A female subject age 78. By self-report, no immunosuppression and no sunbed use. Imaged for a research study, with no referral diagnosis recorded. The patient describes having numerous moles. The patient says their skin tans without first burning:
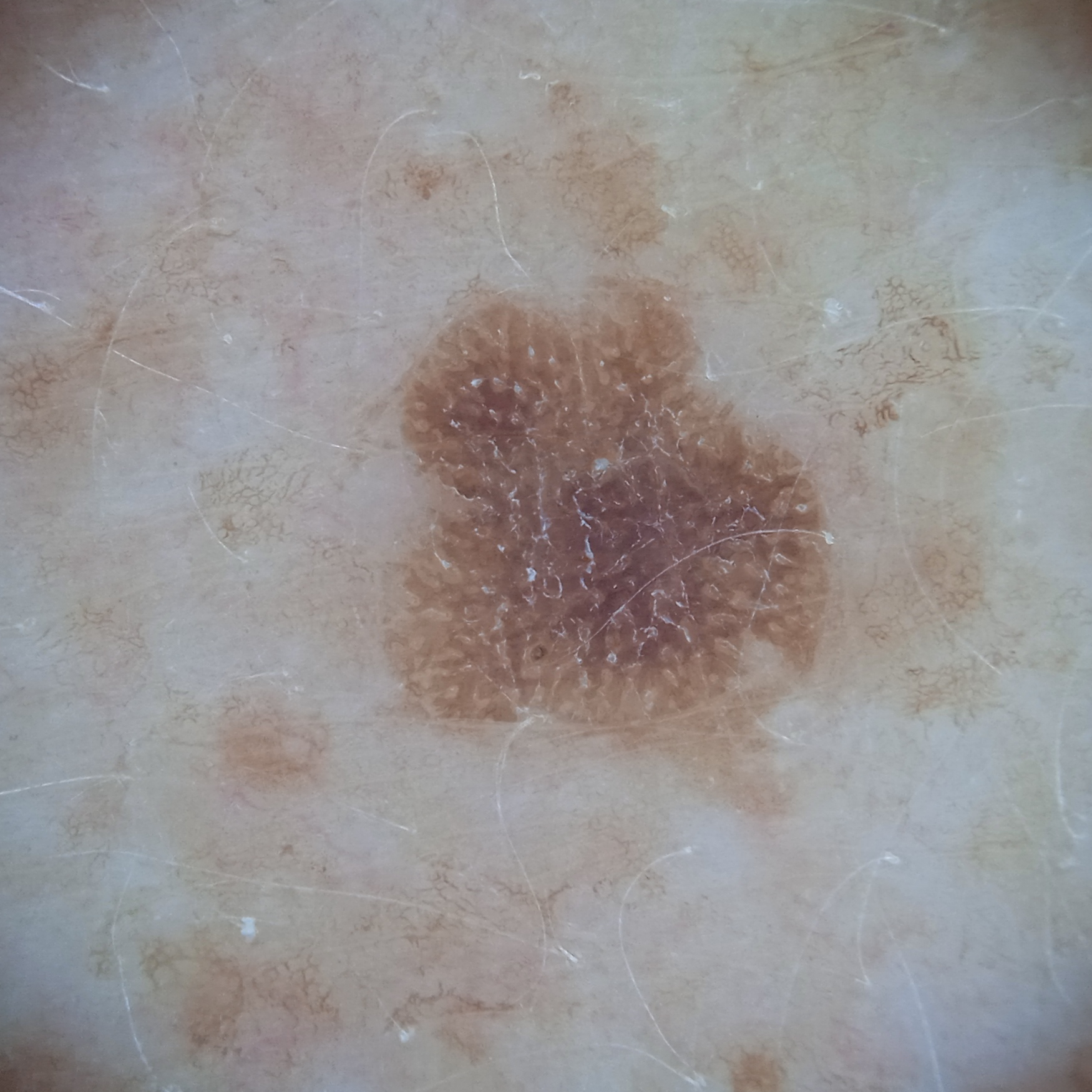Measuring roughly 5.6 mm.
The diagnostic impression was a seborrheic keratosis.